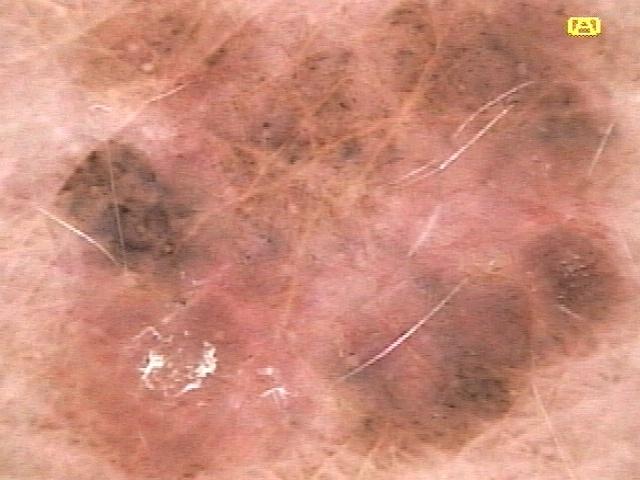Notes:
* risk factors — a previous melanoma
* patient — female, in their mid- to late 60s
* image type — dermoscopy
* body site — the posterior trunk
* diagnostic label — Melanoma (biopsy-proven)